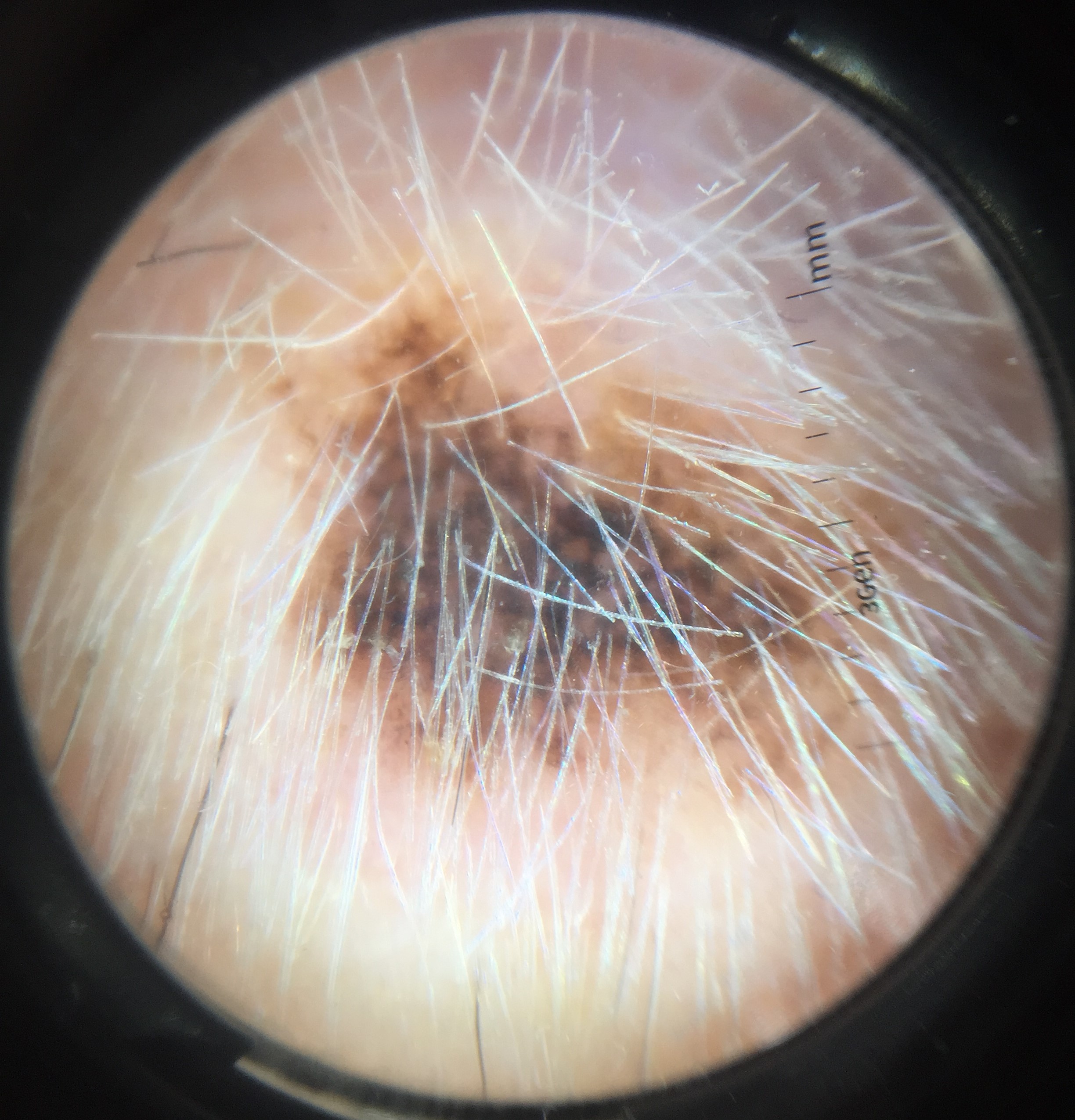Confirmed on histopathology as a melanoma.